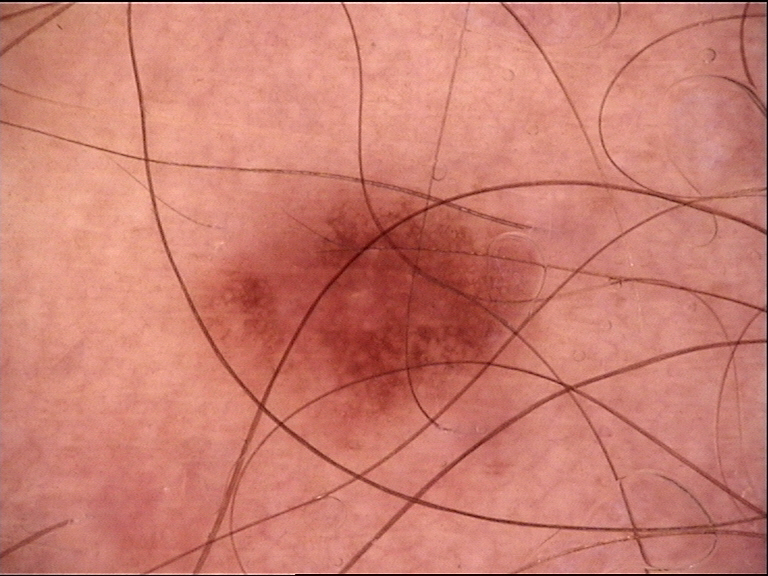{"diagnosis": {"name": "dysplastic junctional nevus", "code": "jd", "malignancy": "benign", "super_class": "melanocytic", "confirmation": "expert consensus"}}